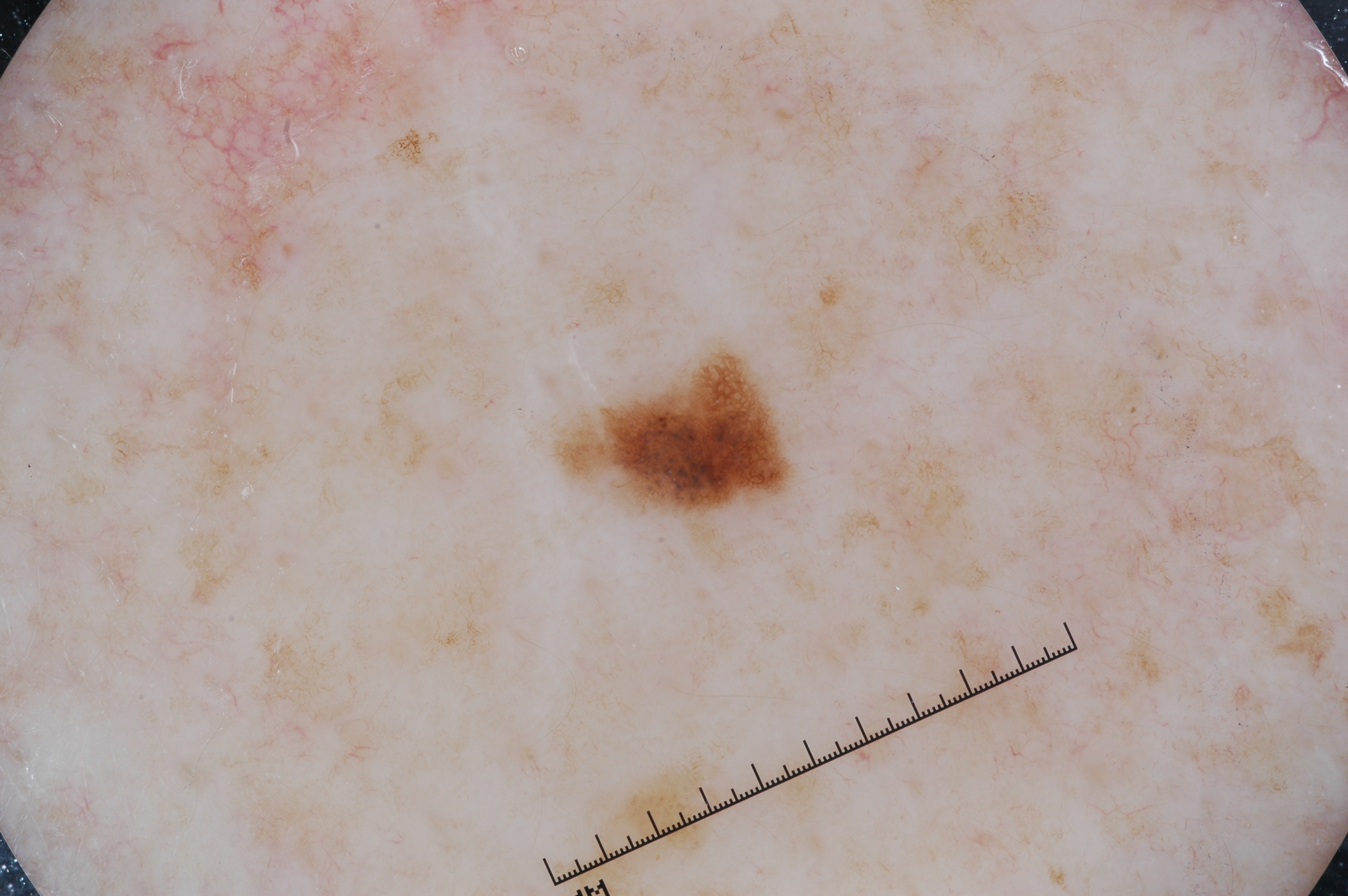<case>
<image>
  <modality>dermoscopy</modality>
</image>
<lesion_location>
  <bbox_xyxy>569, 364, 779, 518</bbox_xyxy>
</lesion_location>
<dermoscopic_features>
  <present>pigment network</present>
  <absent>milia-like cysts, streaks, negative network</absent>
</dermoscopic_features>
<diagnosis>
  <name>melanocytic nevus</name>
  <malignancy>benign</malignancy>
  <lineage>melanocytic</lineage>
  <provenance>clinical</provenance>
</diagnosis>
</case>